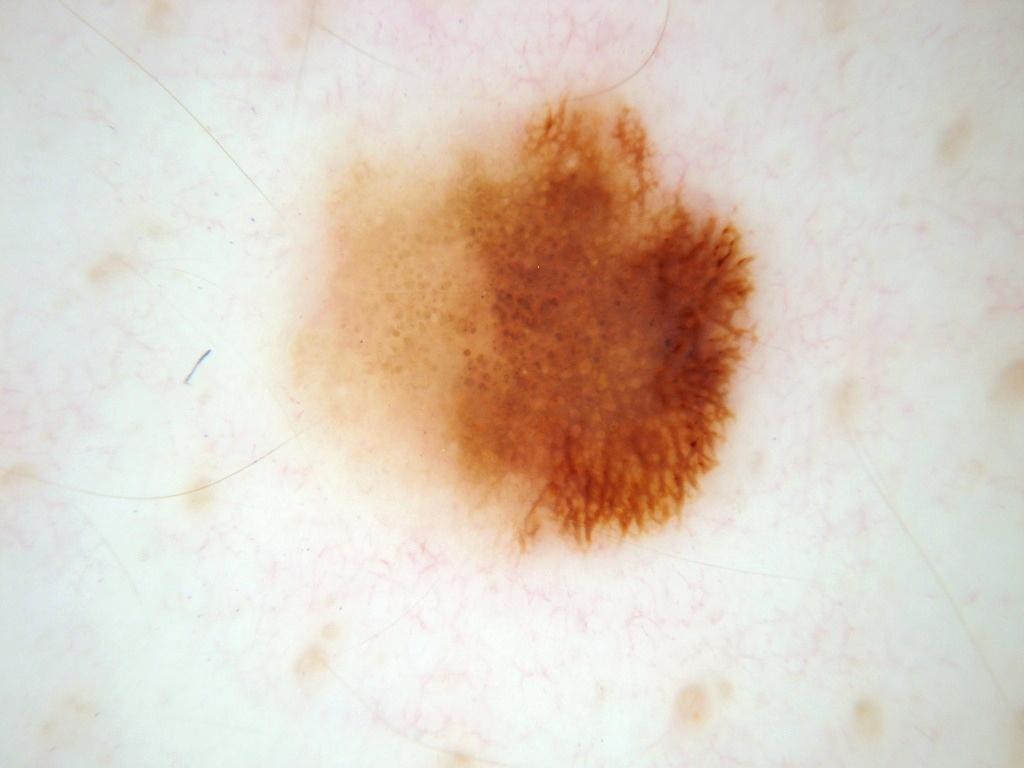Findings:
* imaging — dermoscopy
* subject — male, aged 68 to 72
* lesion bbox — 270, 82, 773, 576
* features — pigment network, globules, and streaks
* impression — a melanocytic nevus, a benign lesion